A dermoscopic image of a skin lesion; a male patient, approximately 70 years of age — 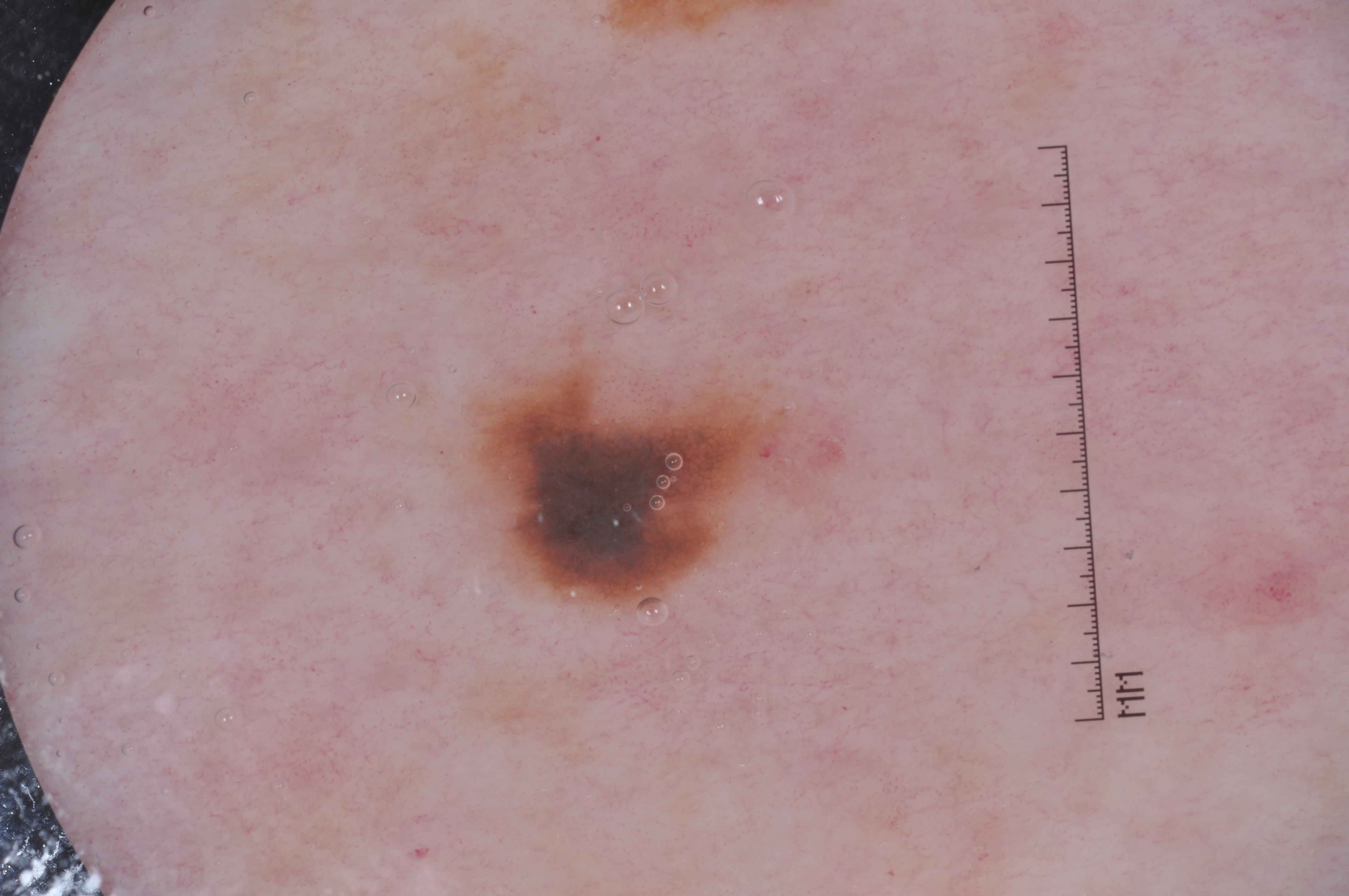As (left, top, right, bottom), the lesion occupies the region [474, 365, 822, 602]. Dermoscopic assessment notes pigment network; no negative network, milia-like cysts, or streaks. A small lesion within a wider field of skin. Consistent with a melanocytic nevus.